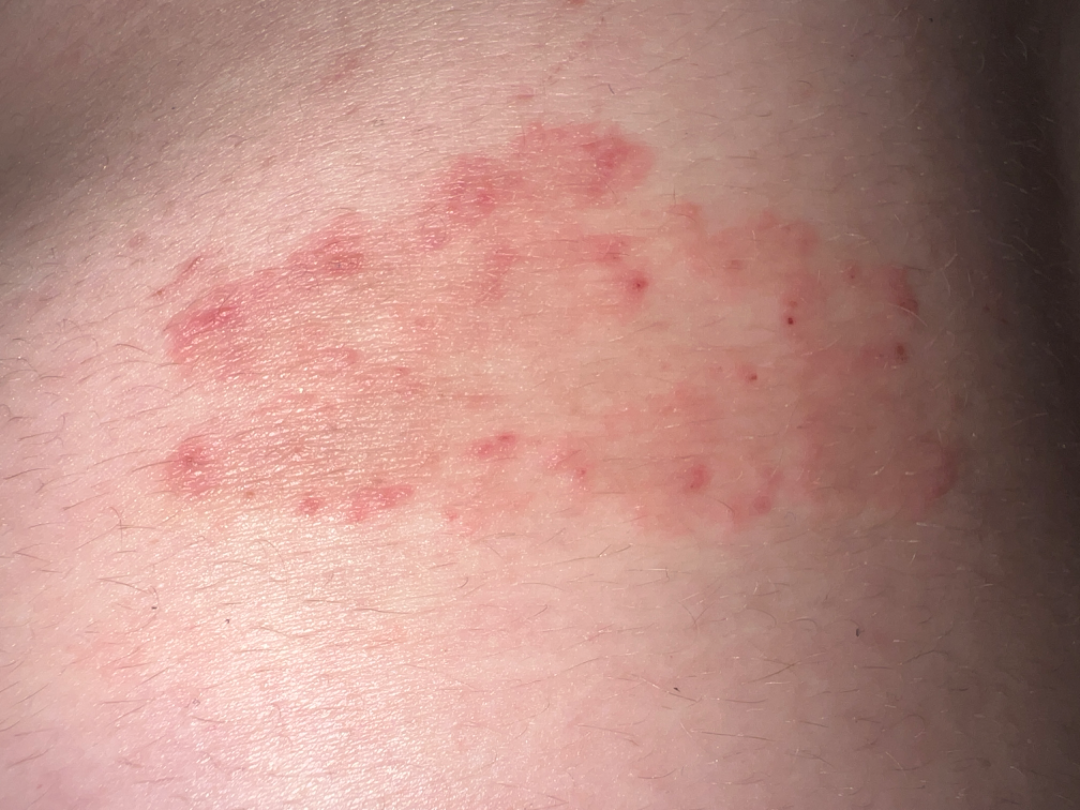Located on the back of the torso.
An image taken at an angle.
Female subject, age 18–29.
One reviewing dermatologist: in keeping with Tinea.